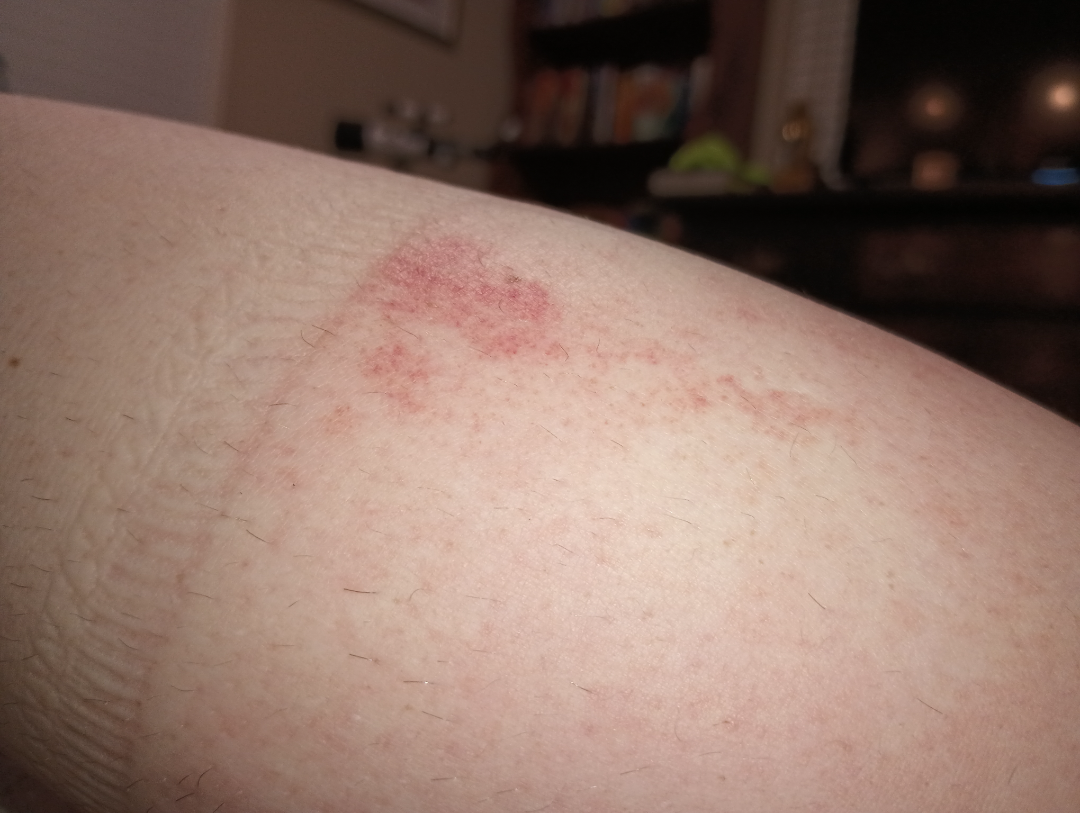assessment: unable to determine
shot_type: at an angle